Close-up view:
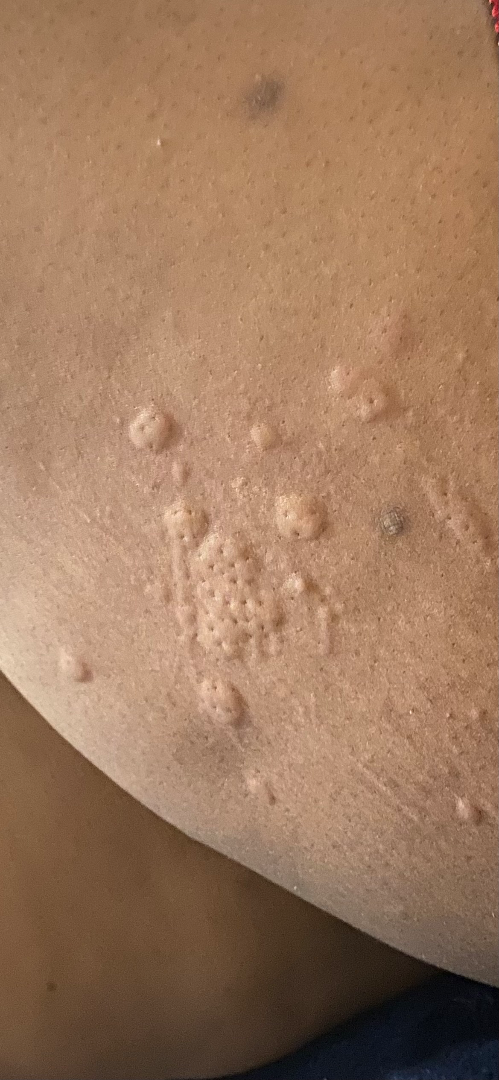Assessment:
On photographic review by a dermatologist, Urticaria (favored).